A subject aged 64. A clinical photograph showing a skin lesion.
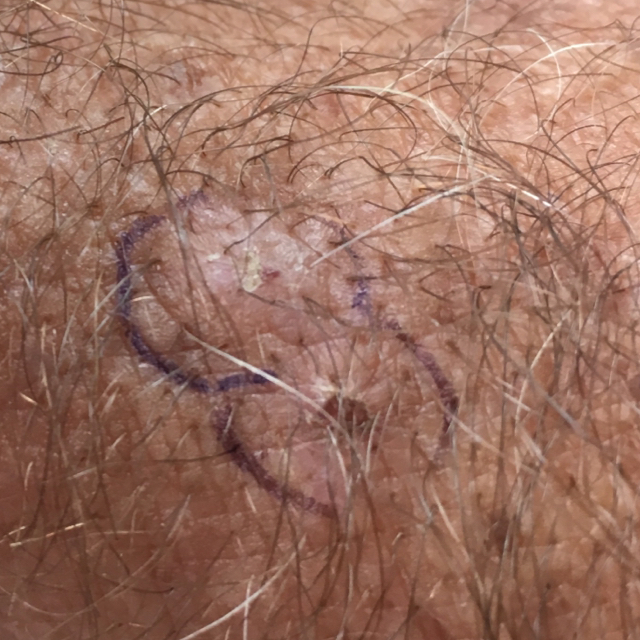| field | value |
|---|---|
| anatomic site | a forearm |
| patient-reported symptoms | itching, bleeding, elevation |
| diagnostic label | actinic keratosis (clinical consensus) |